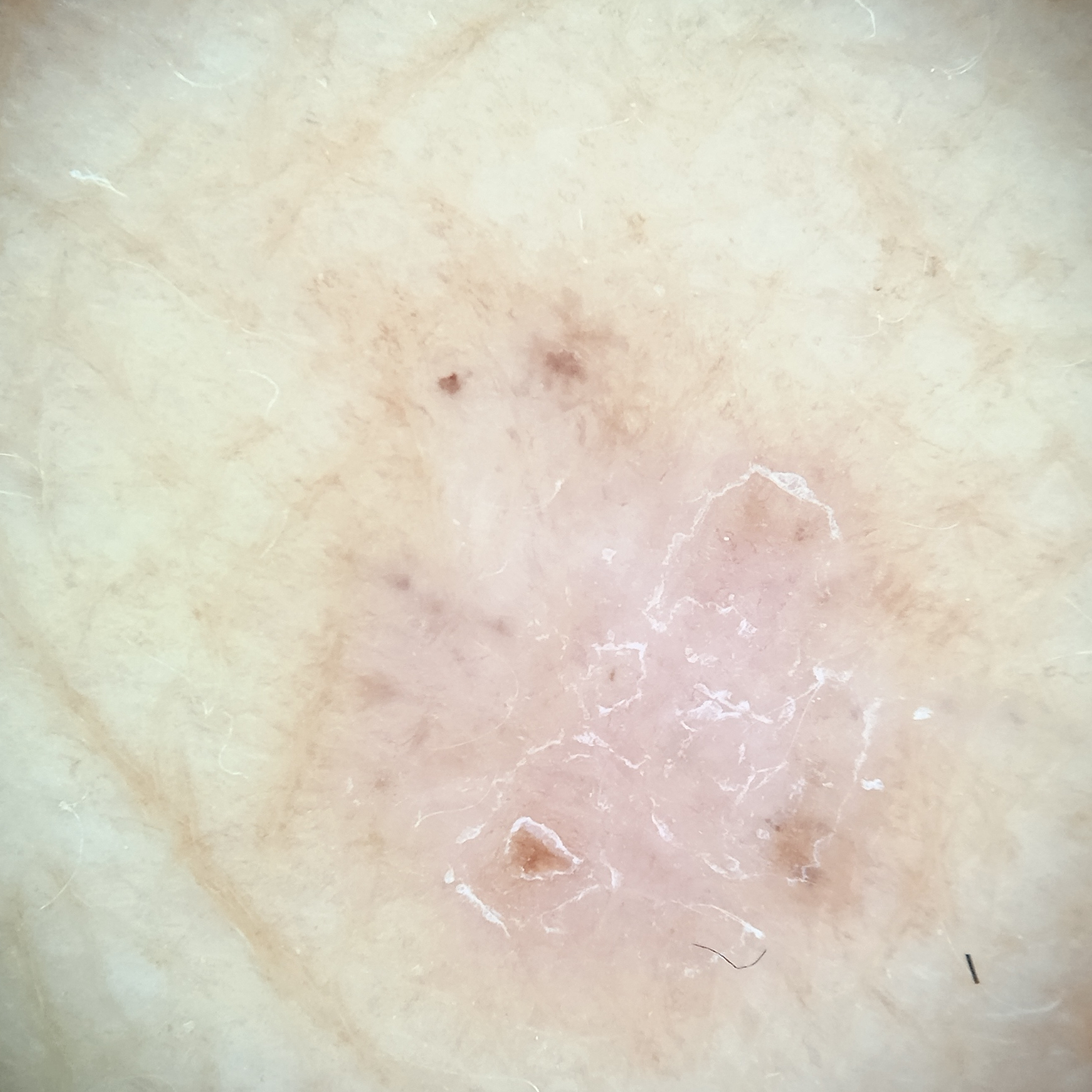<record>
  <patient>
    <age>64</age>
    <sex>female</sex>
  </patient>
  <mole_burden>a moderate number of melanocytic nevi</mole_burden>
  <image>dermoscopy</image>
  <risk_factors>
    <positive>a family history of skin cancer, a personal history of cancer</positive>
    <negative>no sunbed use</negative>
  </risk_factors>
  <sun_reaction>skin tans without first burning</sun_reaction>
  <referral>clinical suspicion of basal cell carcinoma</referral>
  <lesion_location>the torso</lesion_location>
  <lesion_size>
    <diameter_mm>8.1</diameter_mm>
  </lesion_size>
  <diagnosis>
    <name>basal cell carcinoma</name>
    <malignancy>malignant</malignancy>
    <procedure>punch biopsy</procedure>
    <tumor_thickness_mm>0.6</tumor_thickness_mm>
  </diagnosis>
</record>